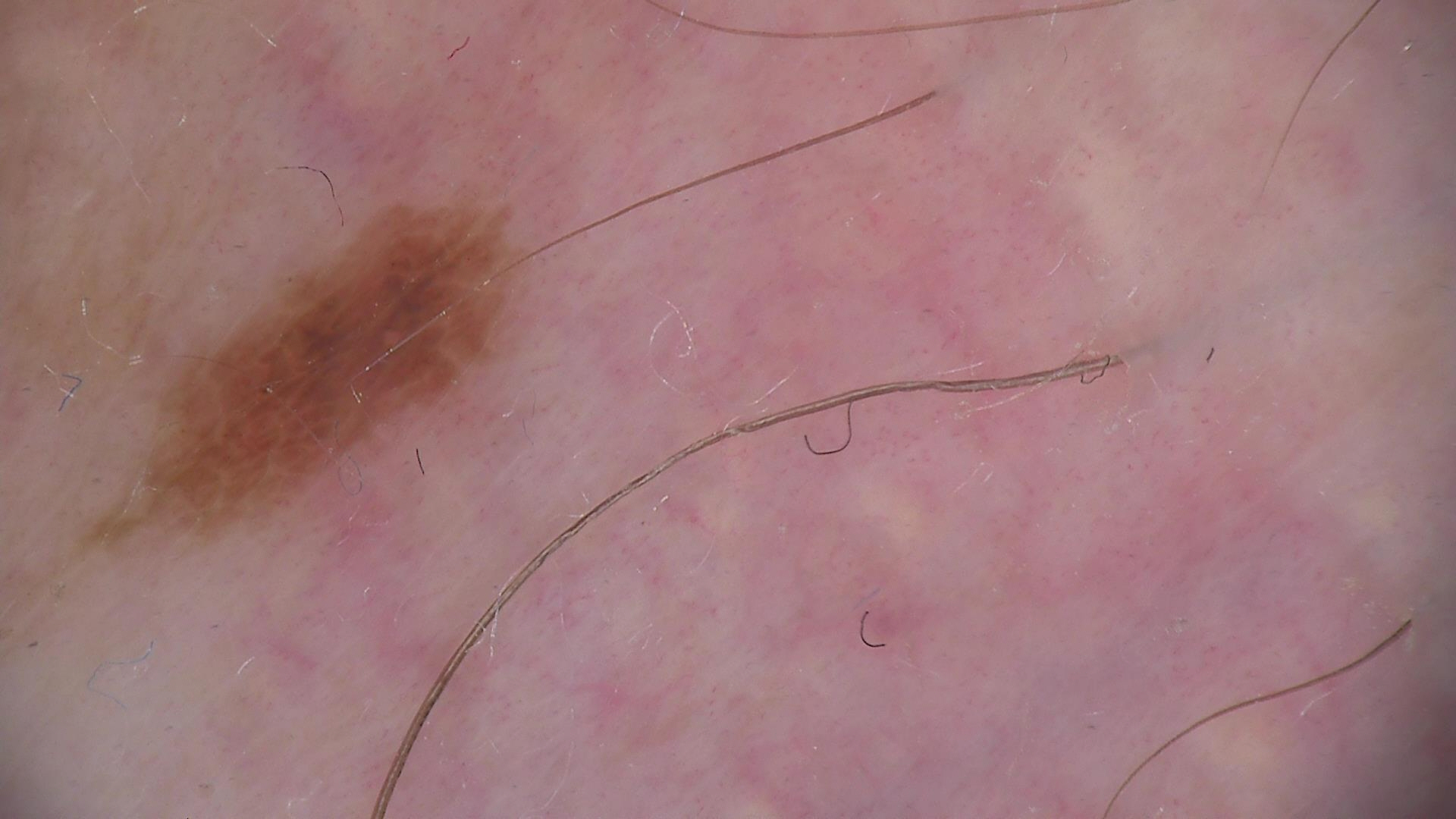Q: What is the imaging modality?
A: dermoscopy
Q: What was the diagnostic impression?
A: dysplastic junctional nevus (expert consensus)